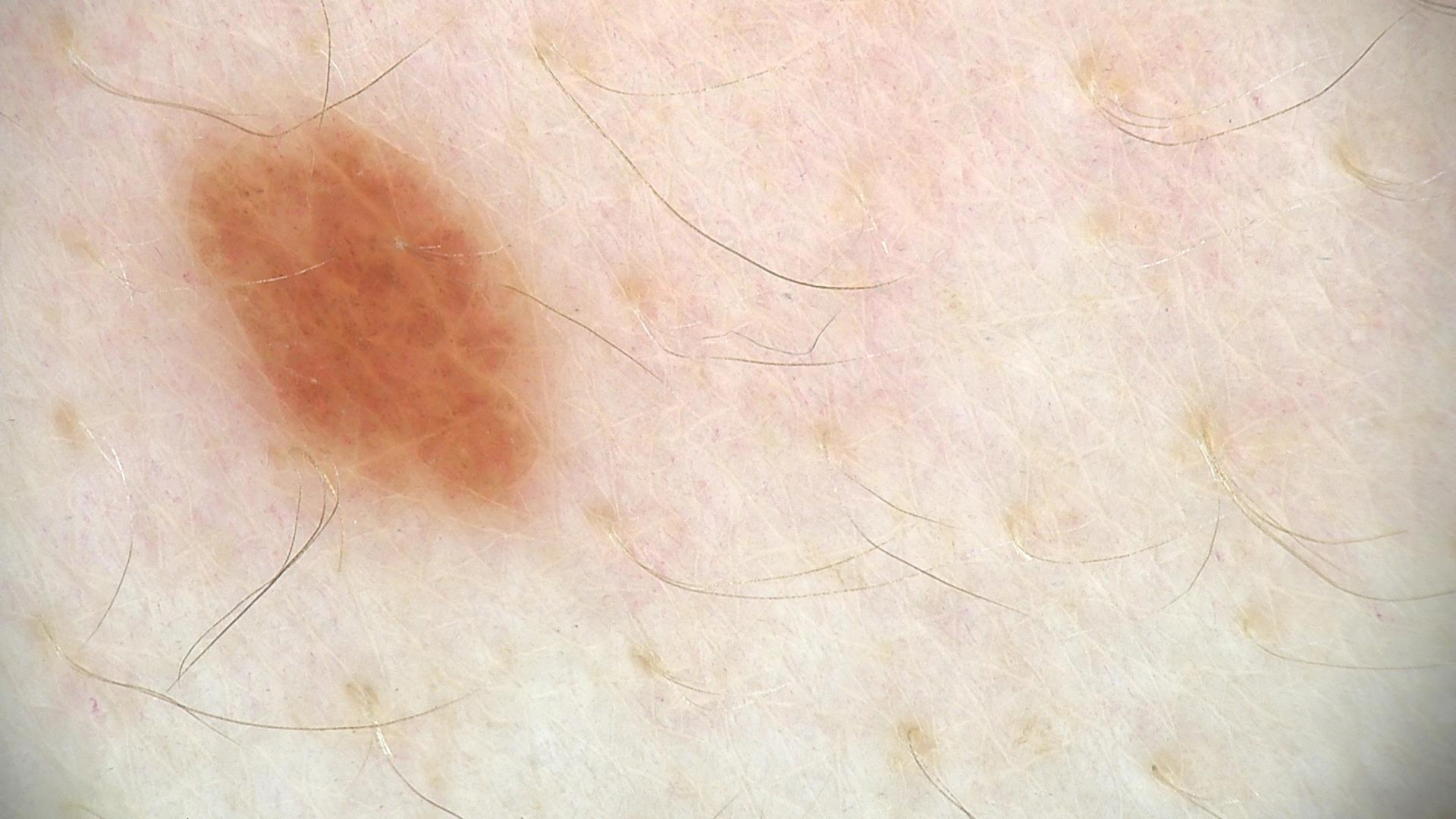imaging — dermatoscopy; label — dysplastic junctional nevus (expert consensus).